The patient reports the condition has been present for one to four weeks · symptoms reported: bleeding, bothersome appearance, itching and enlargement · the photograph is a close-up of the affected area · the lesion is described as raised or bumpy and rough or flaky · self-categorized by the patient as a rash: 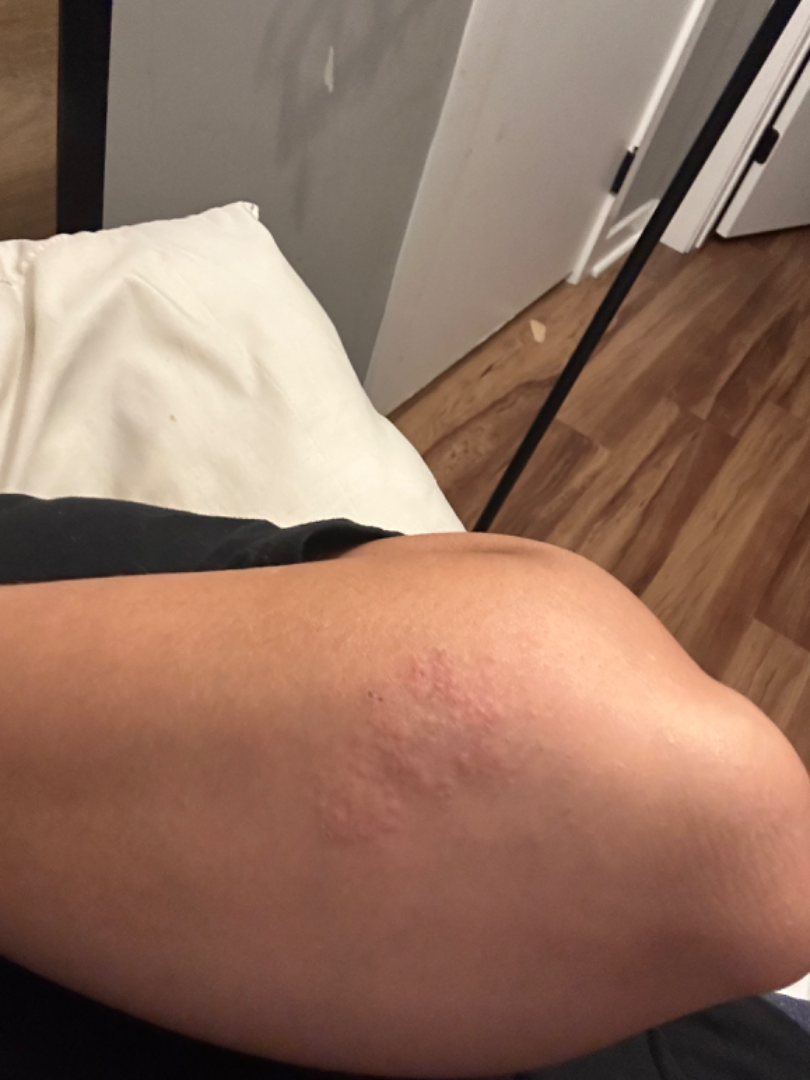diagnostic considerations=consistent with Acute and chronic dermatitis.